A skin lesion imaged with a dermatoscope:
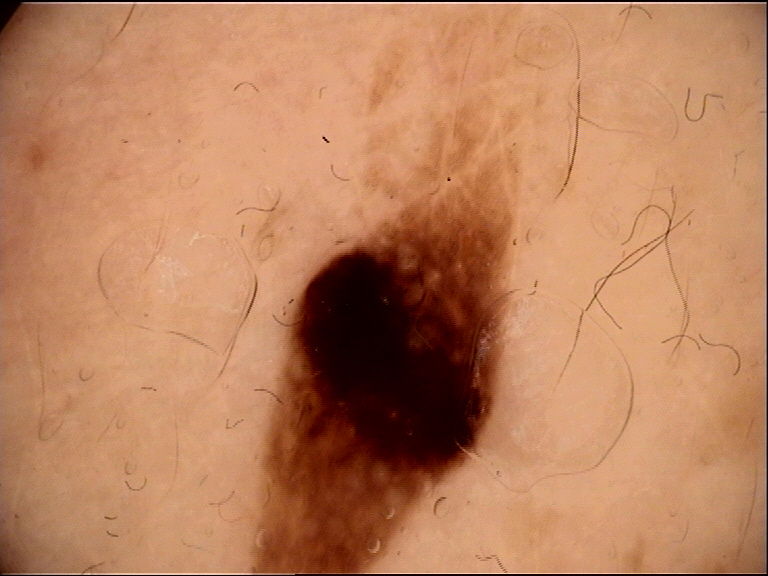  lesion_type:
    main_class: keratinocytic
  diagnosis:
    name: seborrheic keratosis
    code: sk
    malignancy: benign
    super_class: non-melanocytic
    confirmation: expert consensus